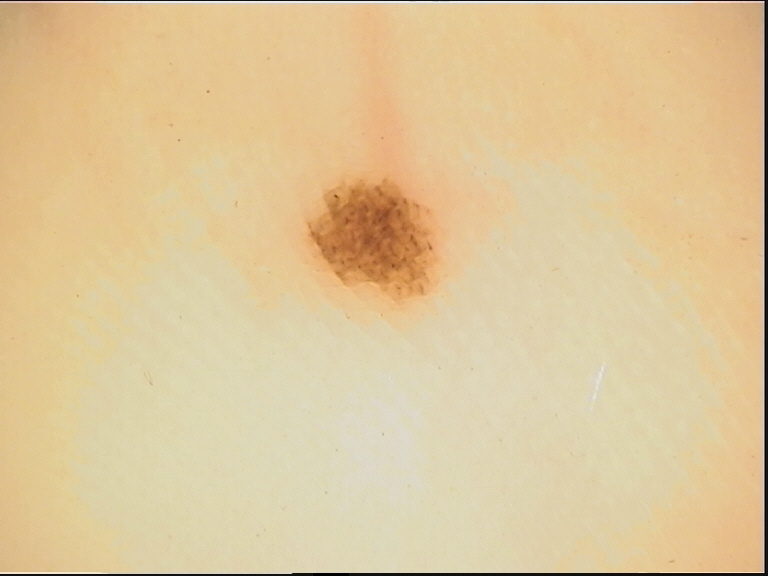image type = dermatoscopy; diagnostic label = acral dysplastic junctional nevus (expert consensus).